A dermoscopic image of a skin lesion.
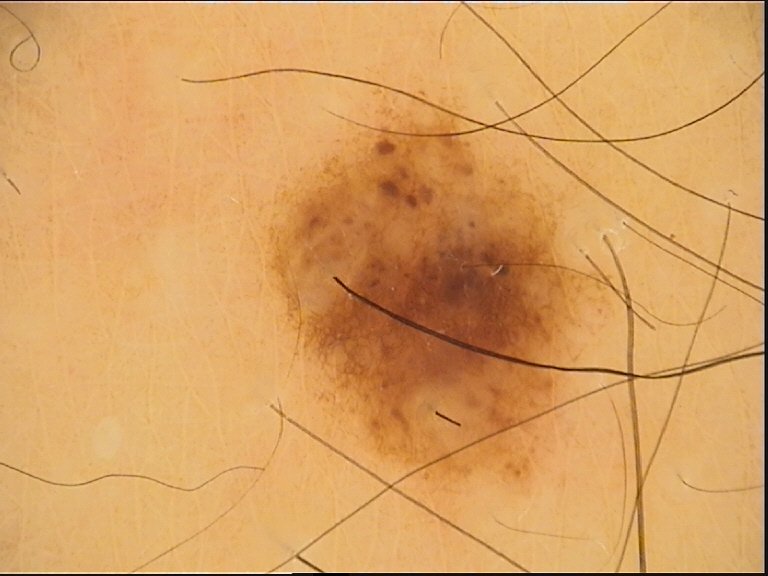Classified as a benign lesion — a dysplastic compound nevus.